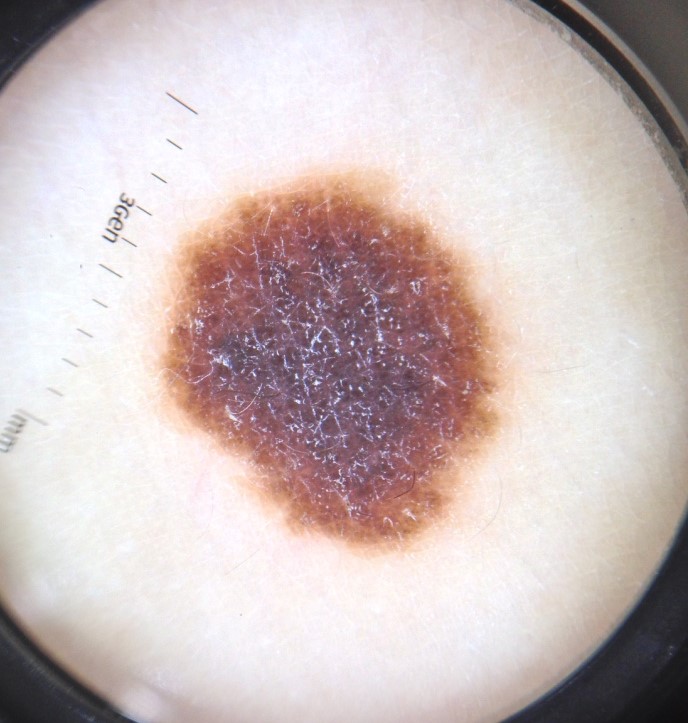| feature | finding |
|---|---|
| diagnosis | congenital compound nevus (expert consensus) |